A dermoscopic image of a skin lesion: 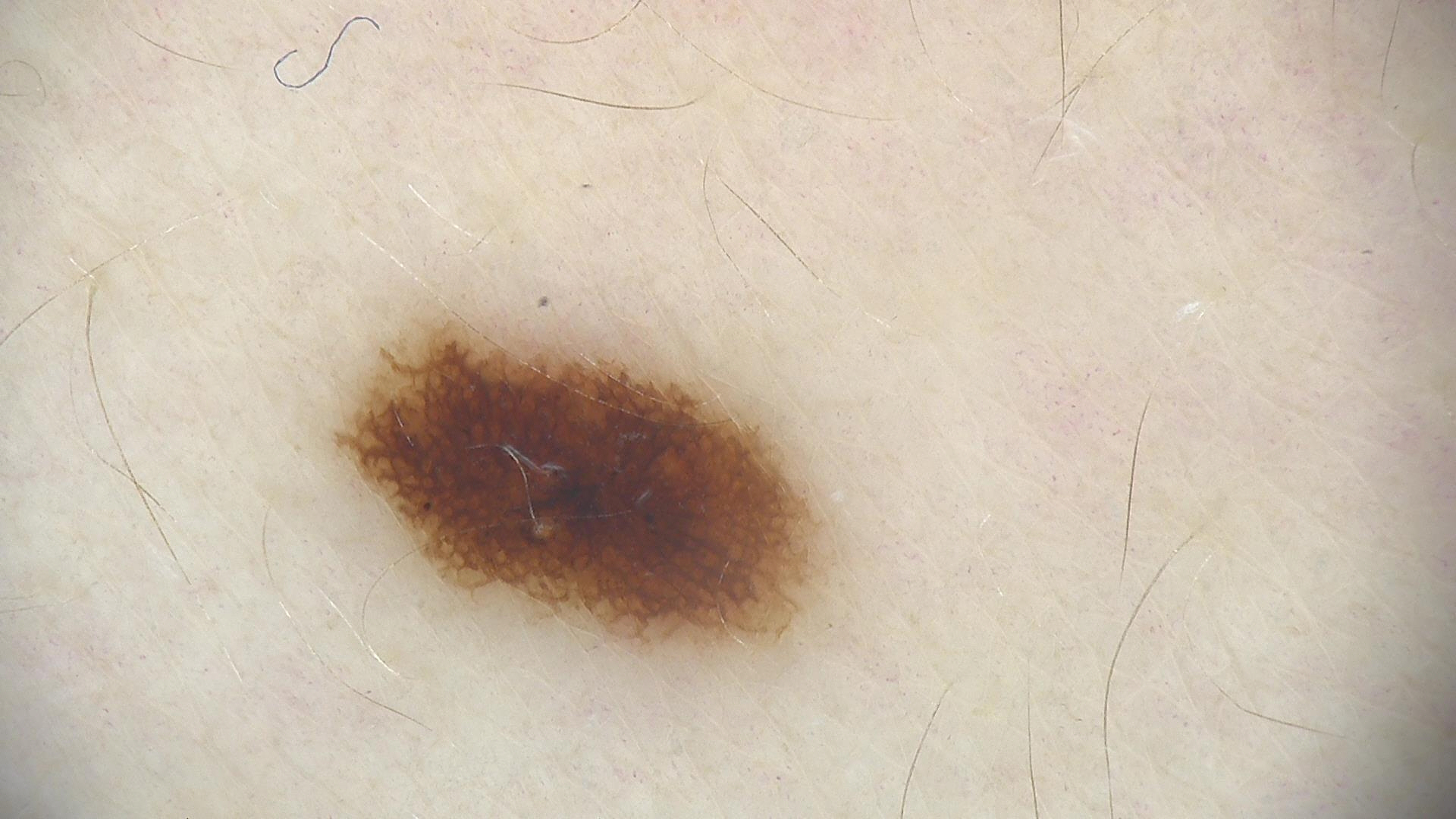Consistent with a dysplastic junctional nevus.